A dermatoscopic image of a skin lesion; on a questionnaire the patient reported a personal history of skin cancer; imaged for a research study, with no referral diagnosis recorded; the patient says their skin reddens with sun exposure; a moderate number of moles by the patient's own estimate; a female patient aged 50:
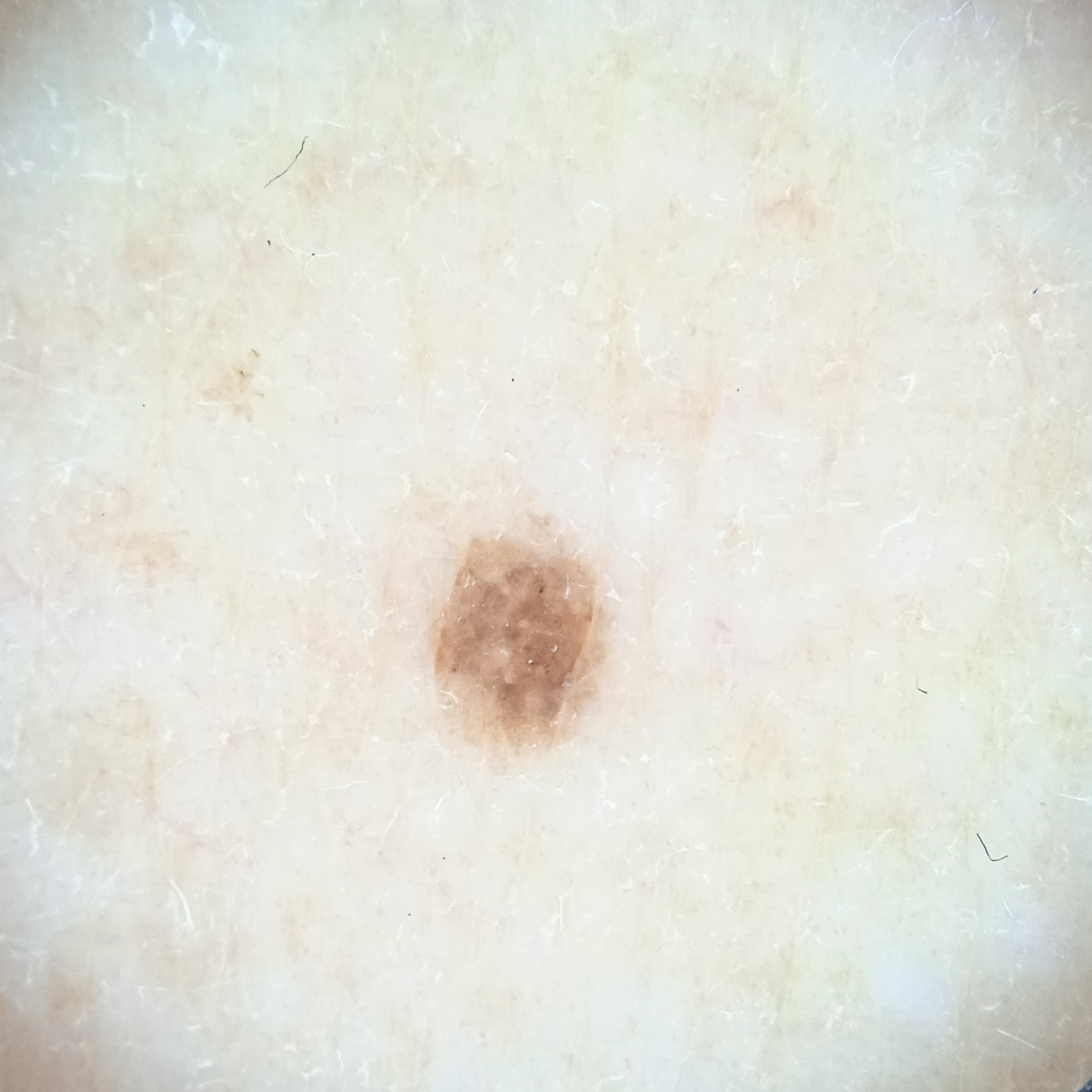Located on an arm. The lesion measures approximately 2.5 mm. The dermatologists' assessment was a melanocytic nevus.